A dermoscopy image of a single skin lesion.
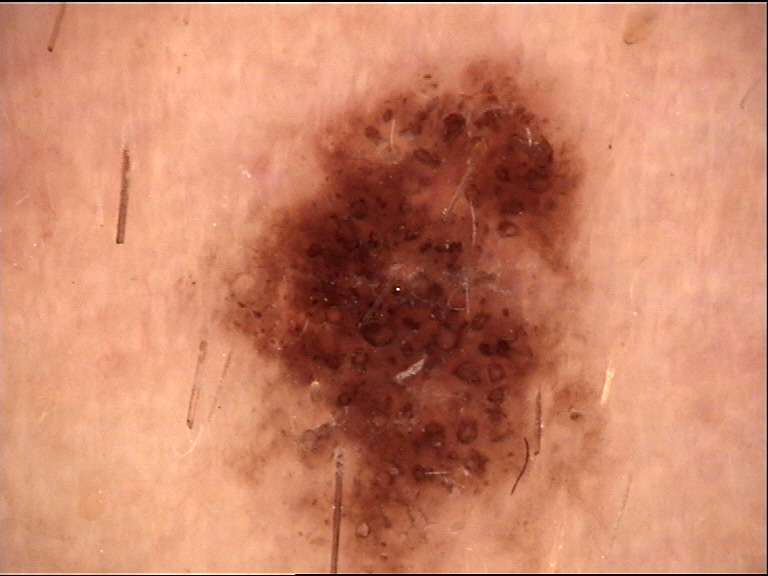Q: What was the diagnostic impression?
A: congenital compound nevus (expert consensus)